Female contributor, age 50–59 · the photo was captured at a distance:
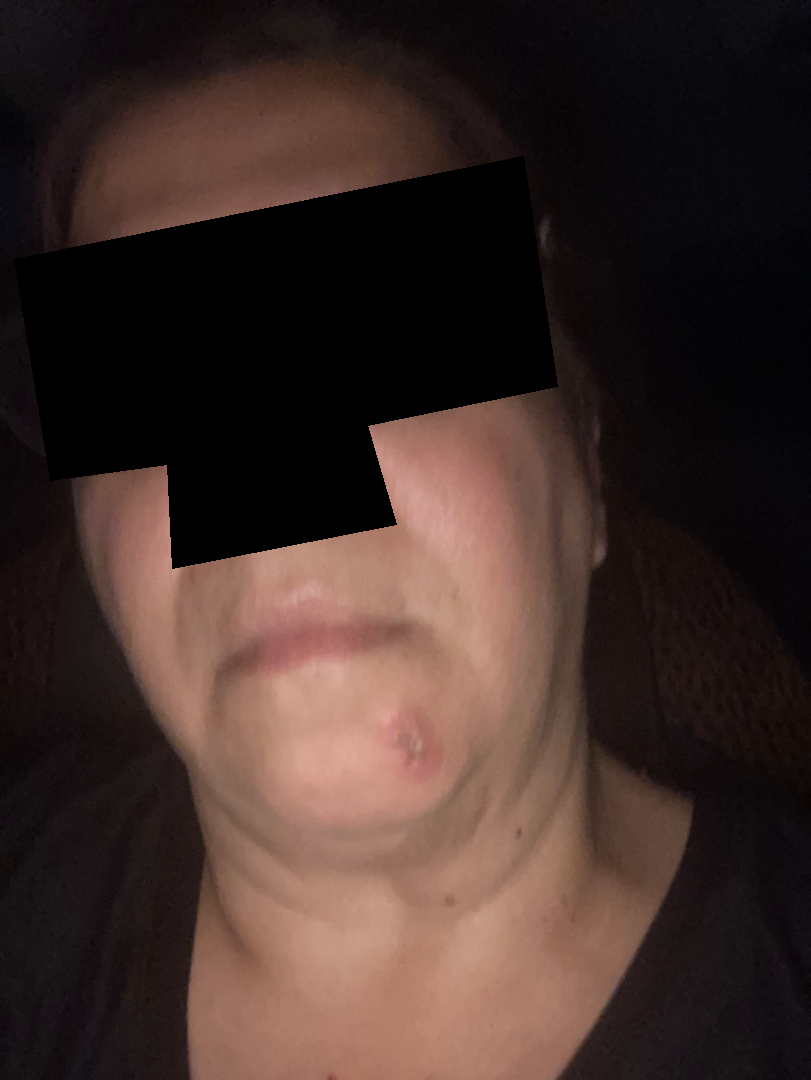No constitutional symptoms were reported. Reported lesion symptoms include pain and itching. Present for about one day. Texture is reported as raised or bumpy. On dermatologist assessment of the image, Abscess, skin cyst and Odontogenic keratocyst were each considered, in no particular order.